A dermoscopic image of a skin lesion:
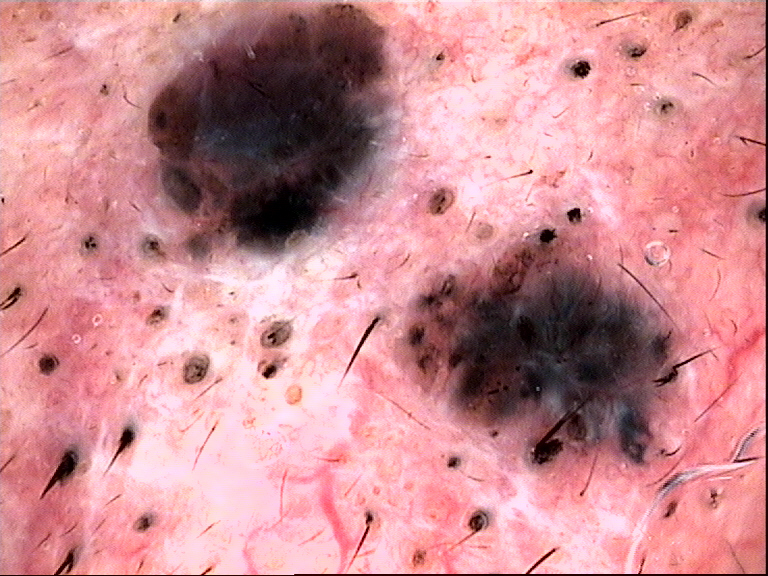Diagnosis:
Histopathology confirmed a keratinocytic lesion — a basal cell carcinoma.